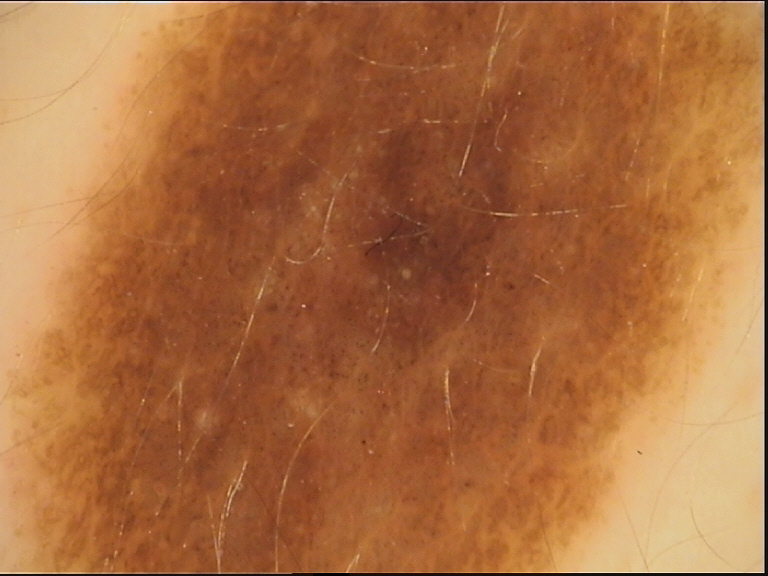A dermatoscopic image of a skin lesion. Labeled as a dysplastic compound nevus.